Dermoscopy of a skin lesion:
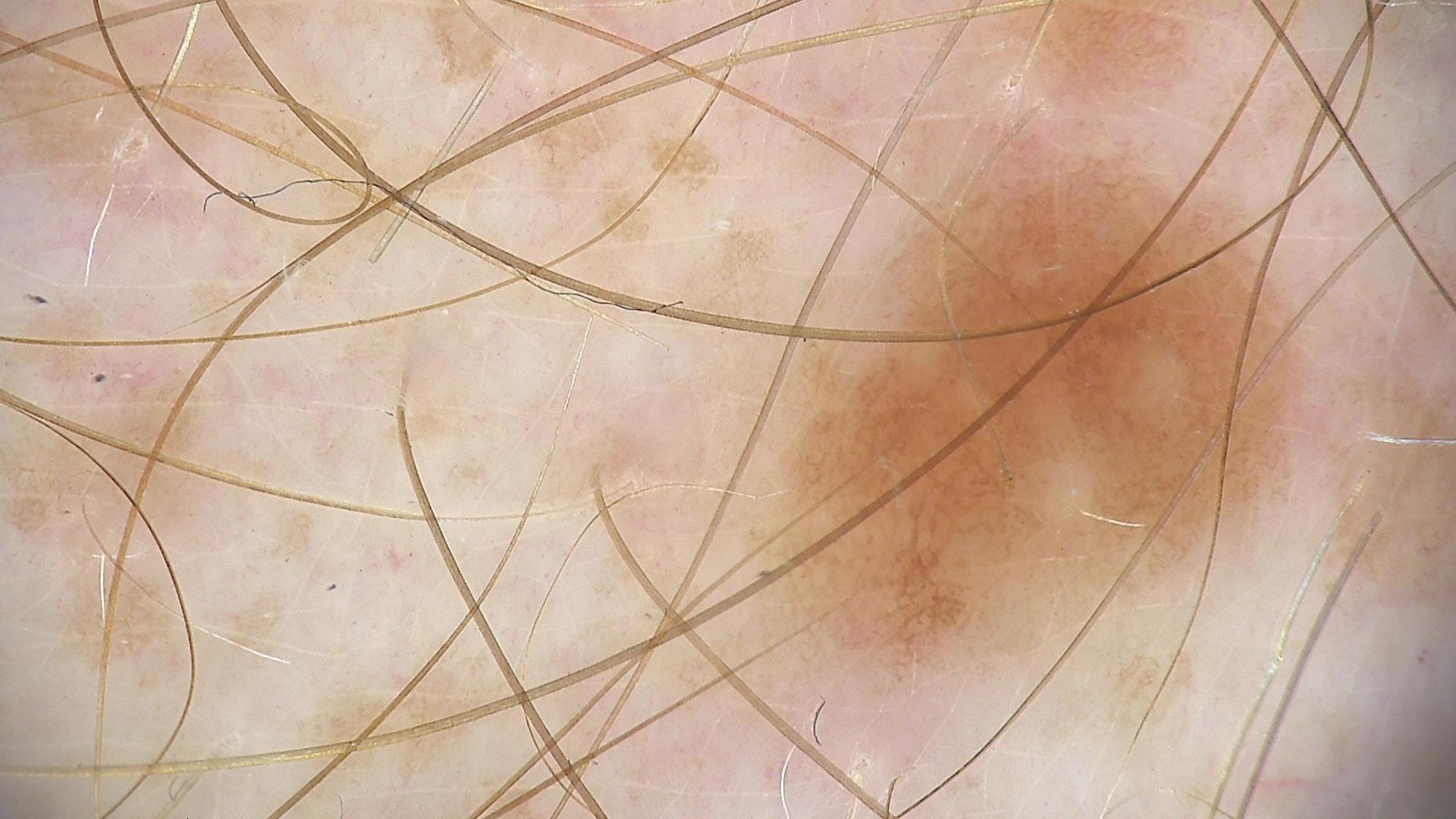Impression:
Diagnosed as a dysplastic junctional nevus.